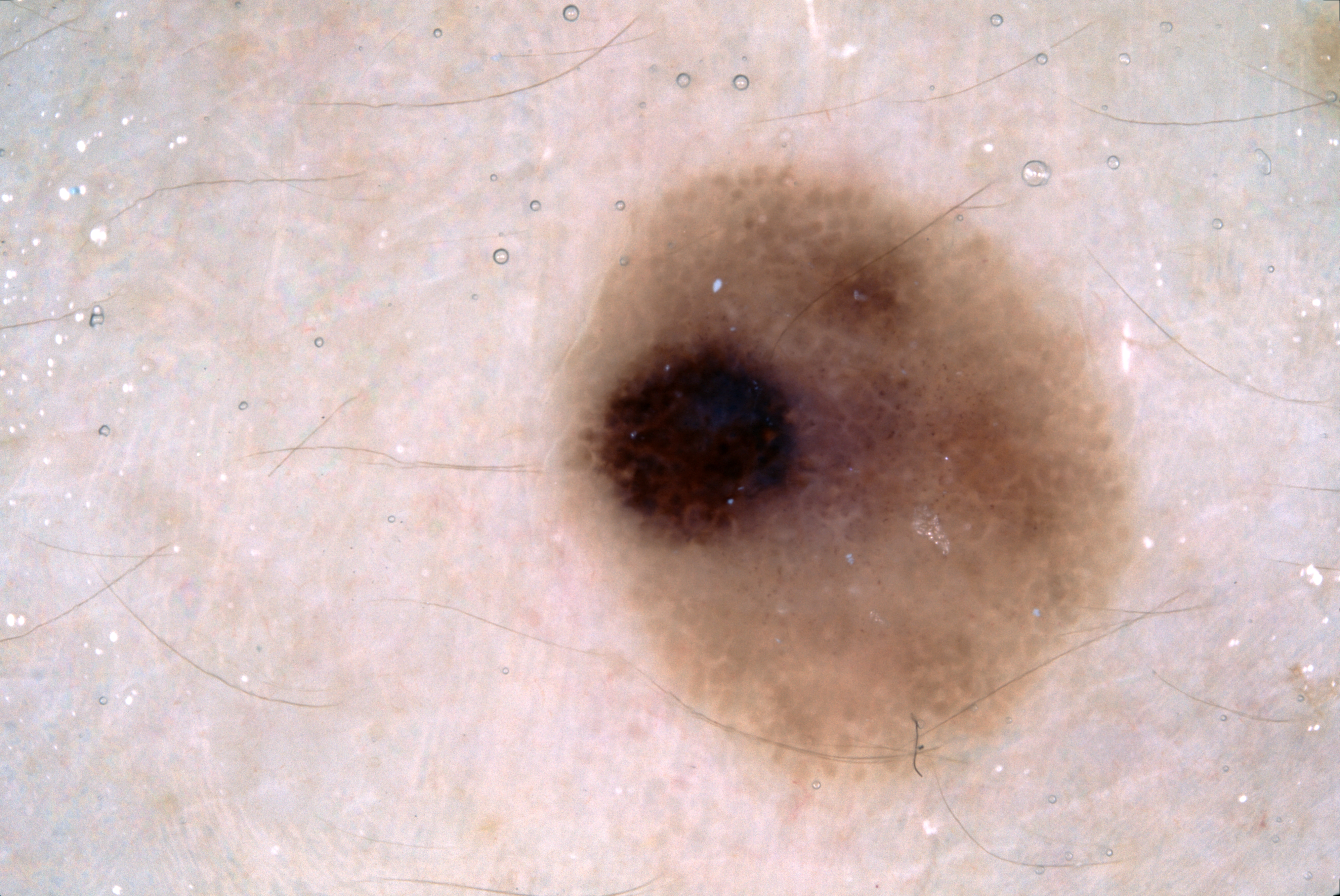| field | value |
|---|---|
| image type | dermatoscopic image of a skin lesion |
| patient | female |
| bounding box | <box>566, 161, 1131, 784</box> |
| dermoscopic findings | milia-like cysts and negative network |
| size | moderate |
| assessment | a melanoma |